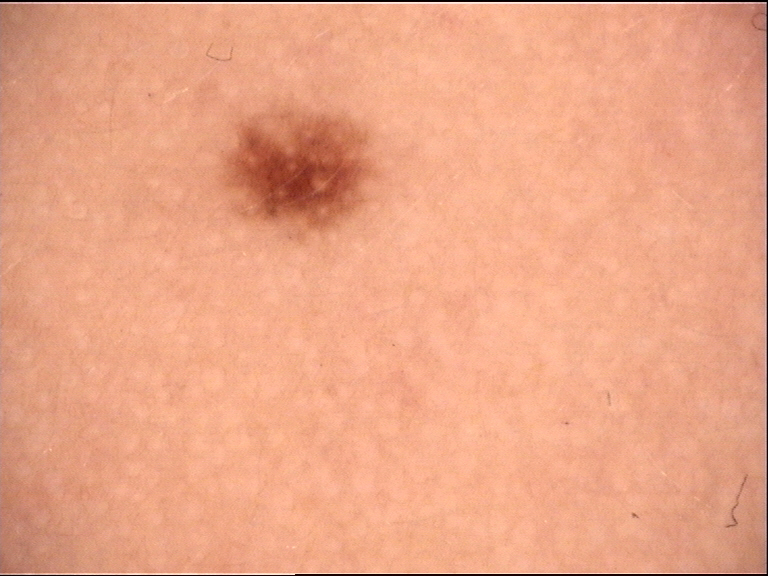A dermoscopic image of a skin lesion.
This is a banal, compound lesion.
Consistent with a Miescher nevus.